Dermoscopy of a skin lesion: 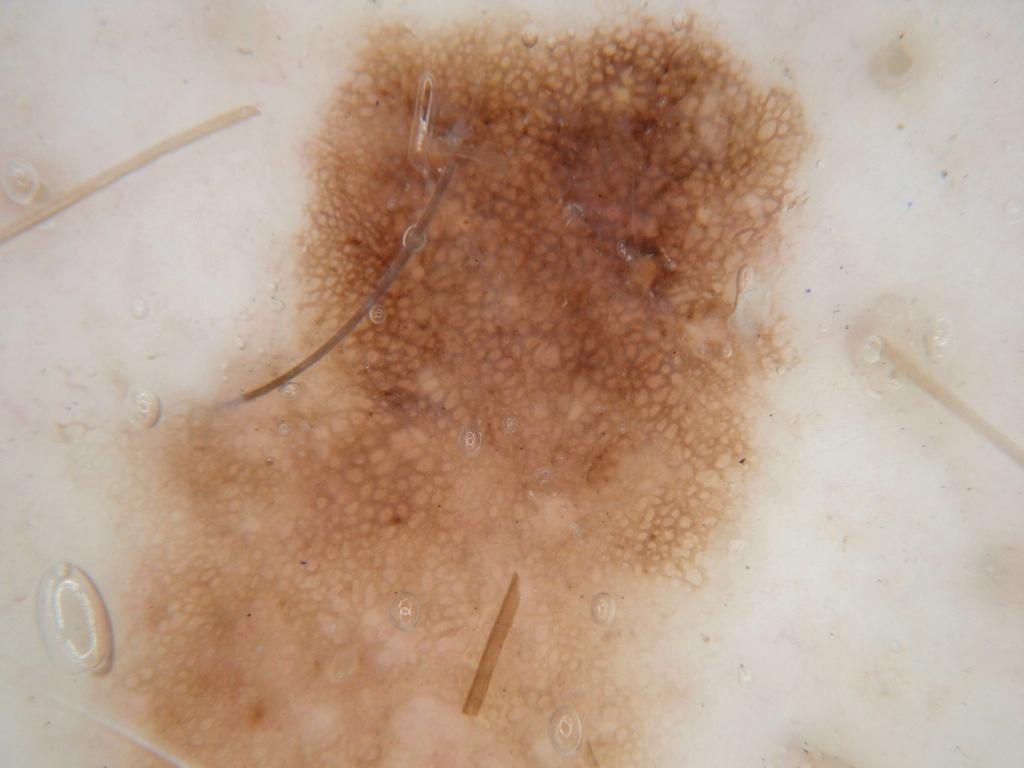lesion bbox: bbox(99, 0, 829, 764)
diagnostic label: a benign lesion